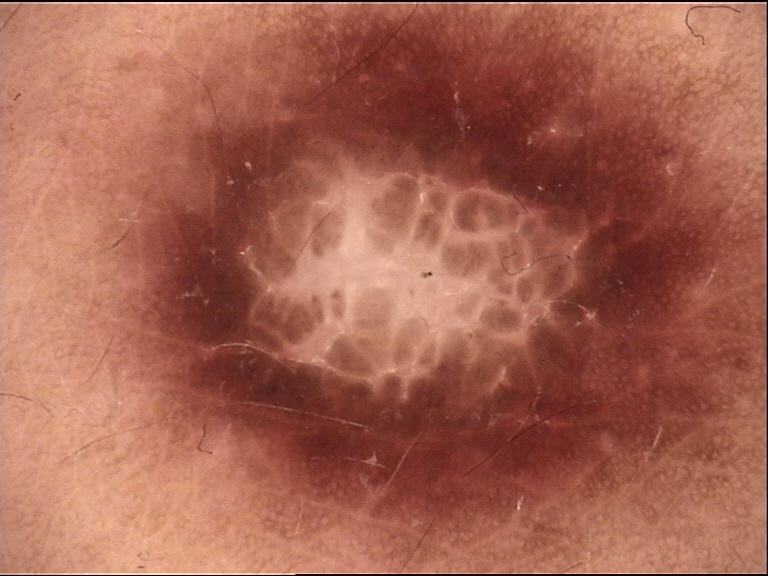category: fibro-histiocytic, class: dermatofibroma (expert consensus).